The contributor is 60–69, female; the lesion involves the arm; this is a close-up image: 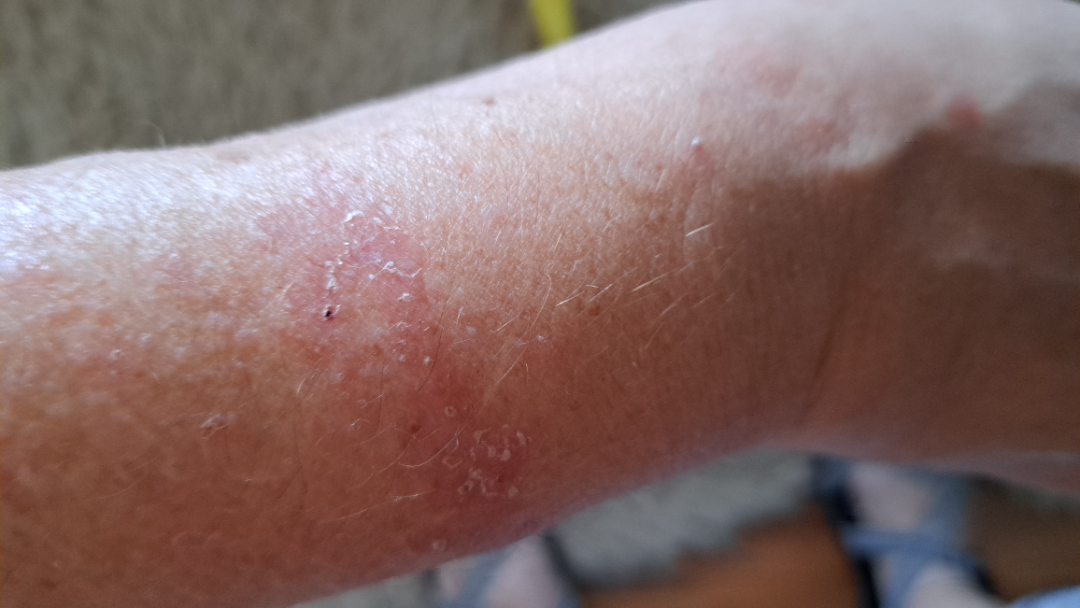{"differential": {"tied_lead": ["Allergic Contact Dermatitis", "Irritant Contact Dermatitis"]}}